A skin lesion imaged with a dermatoscope:
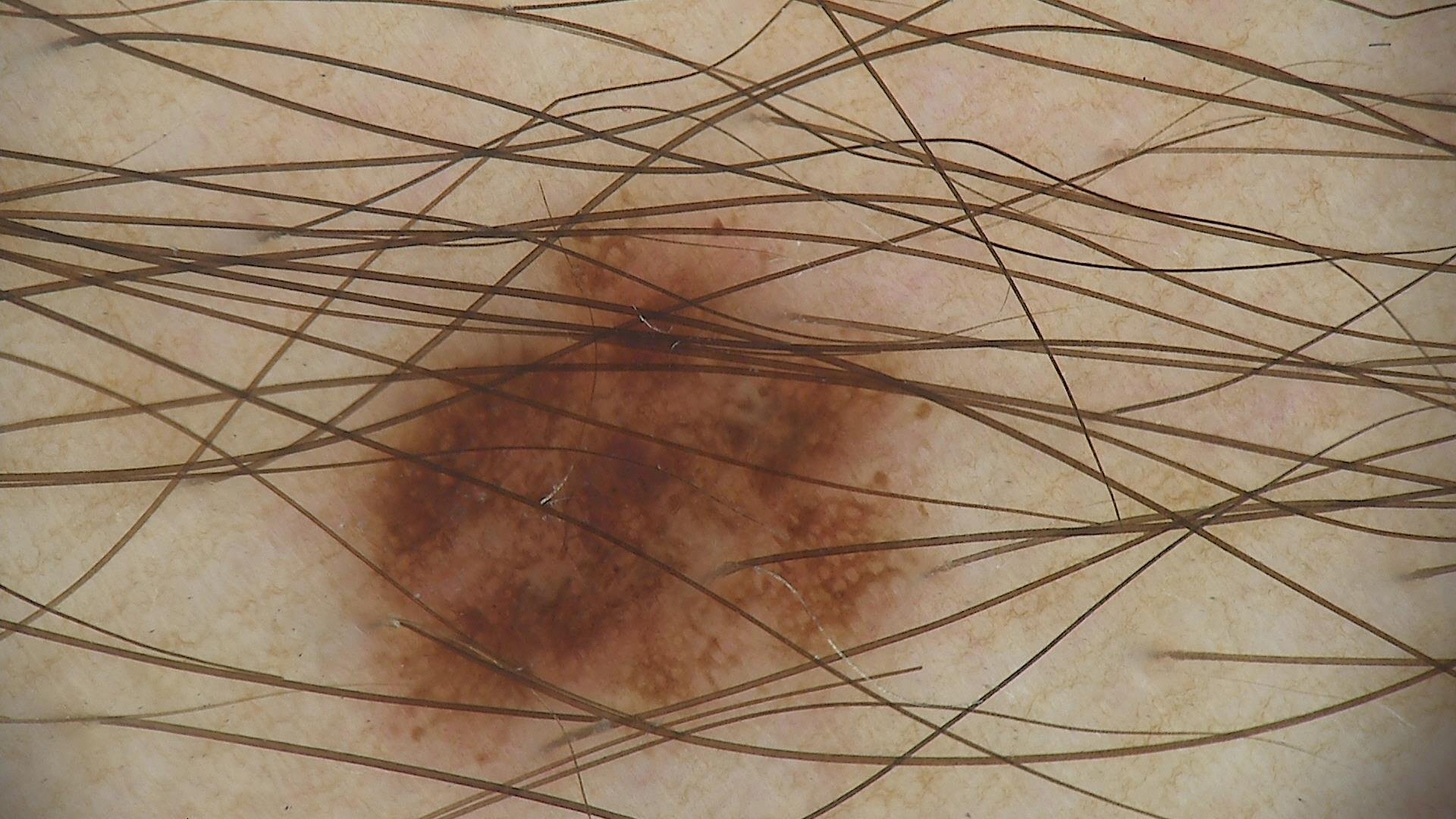{
  "diagnosis": {
    "name": "dysplastic junctional nevus",
    "code": "jd",
    "malignancy": "benign",
    "super_class": "melanocytic",
    "confirmation": "expert consensus"
  }
}